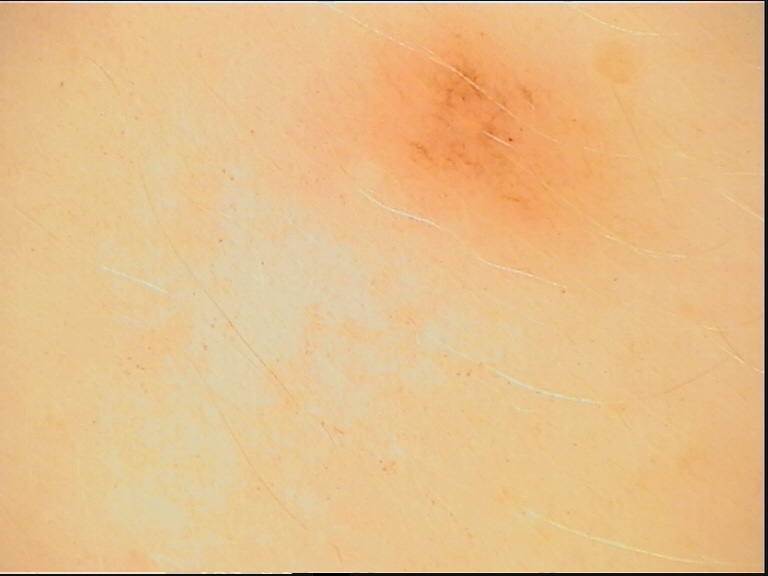Impression: Consistent with a dysplastic junctional nevus.